A clinical photo of a skin lesion taken with a smartphone · a subject in their early 30s: 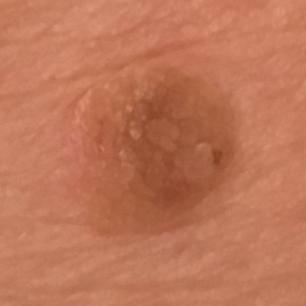location: an arm, symptoms: elevation, assessment: seborrheic keratosis (clinical consensus).